A skin lesion imaged with a dermatoscope.
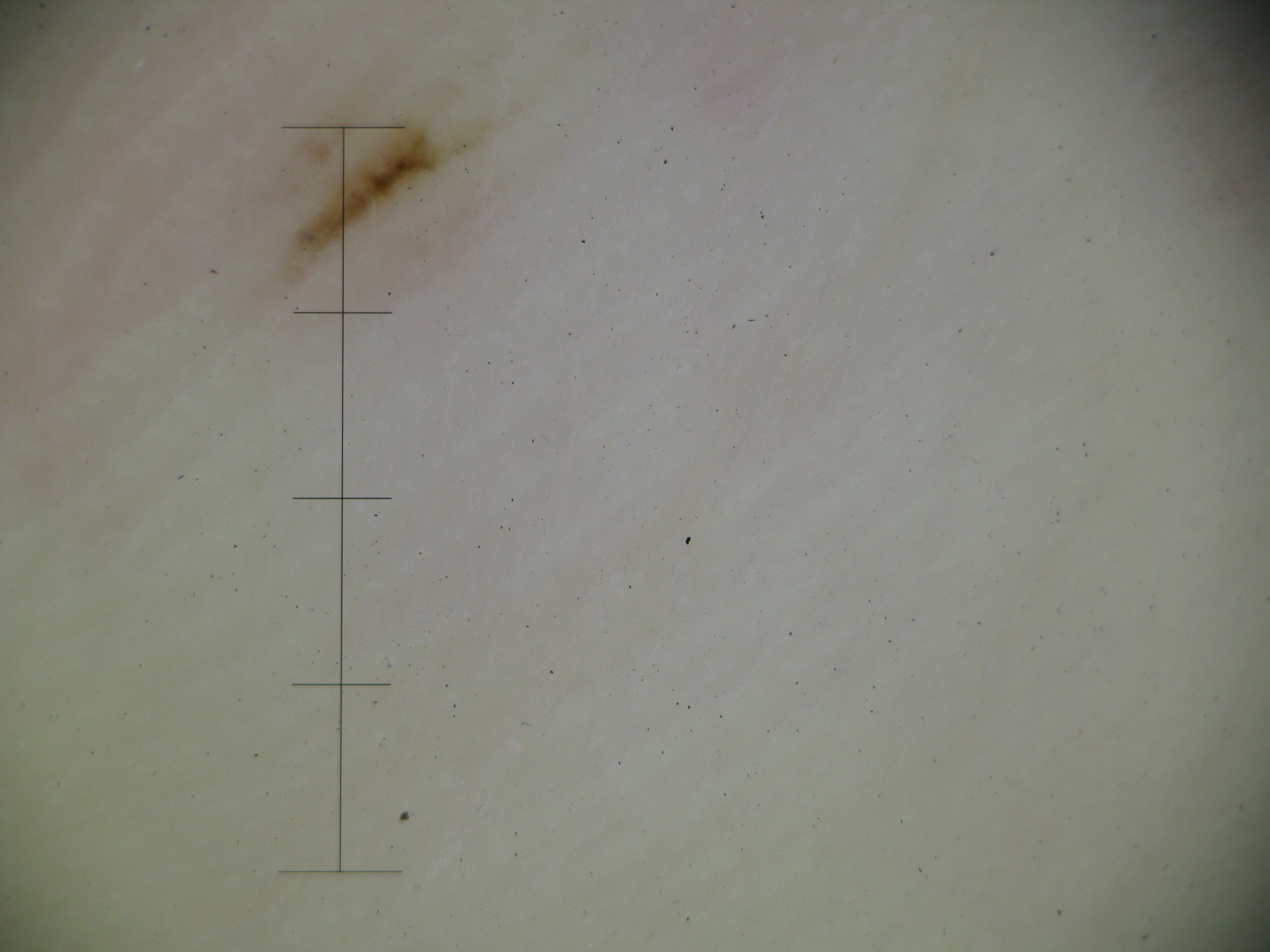This is a banal lesion. Consistent with an acral junctional nevus.